A female patient aged 64 · the referring clinician suspected seborrheic keratosis · a dermatoscopic image of a skin lesion — 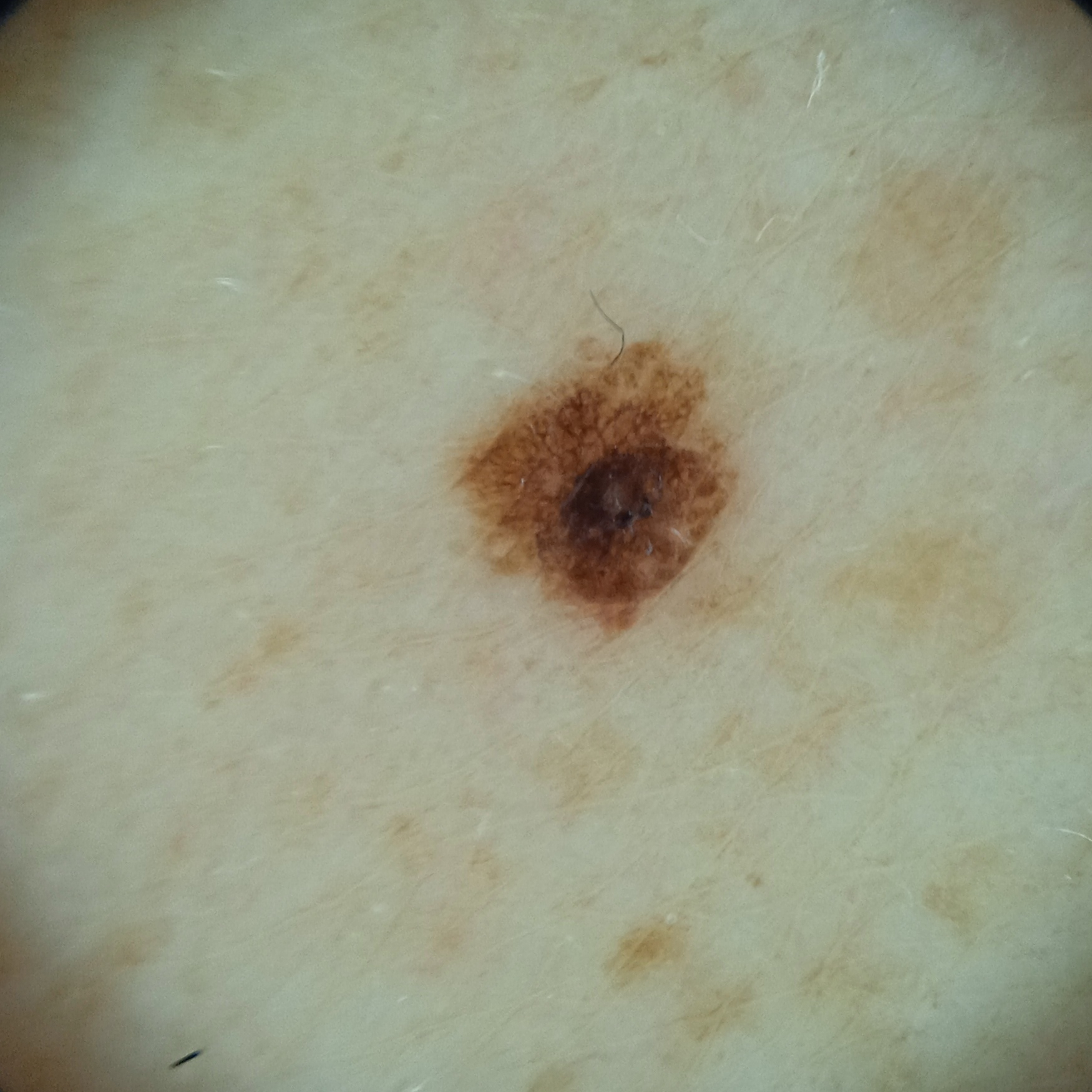location: the back | lesion size: 3.5 mm | diagnosis: seborrheic keratosis (biopsy-proven).